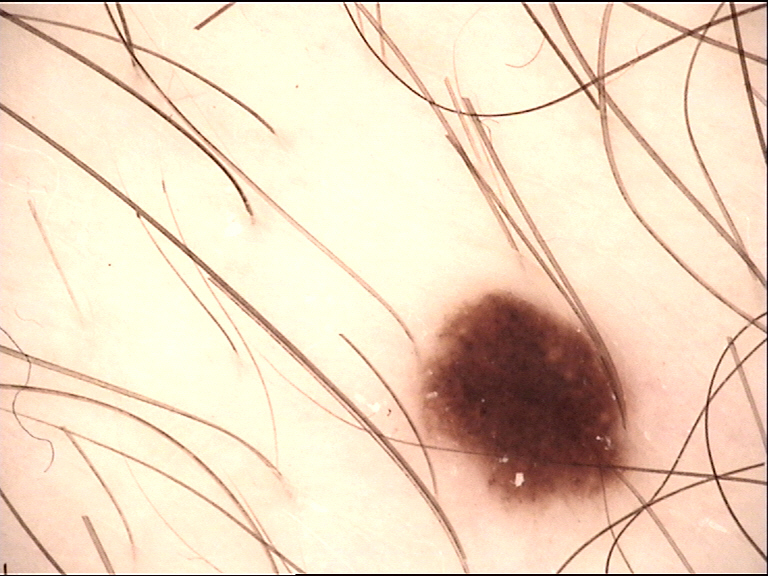Findings:
A skin lesion imaged with a dermatoscope.
Impression:
The diagnosis was a banal lesion — a junctional nevus.